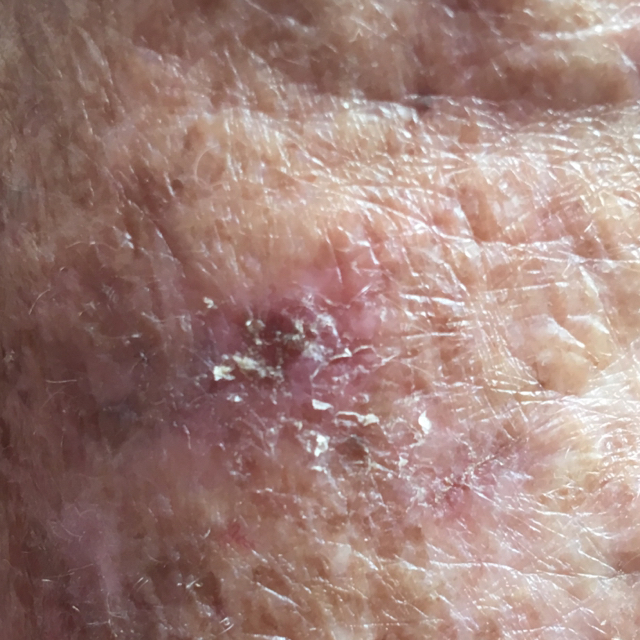impression = actinic keratosis (clinical consensus).